Male patient, age 40–49; the lesion involves the back of the hand; an image taken at a distance: 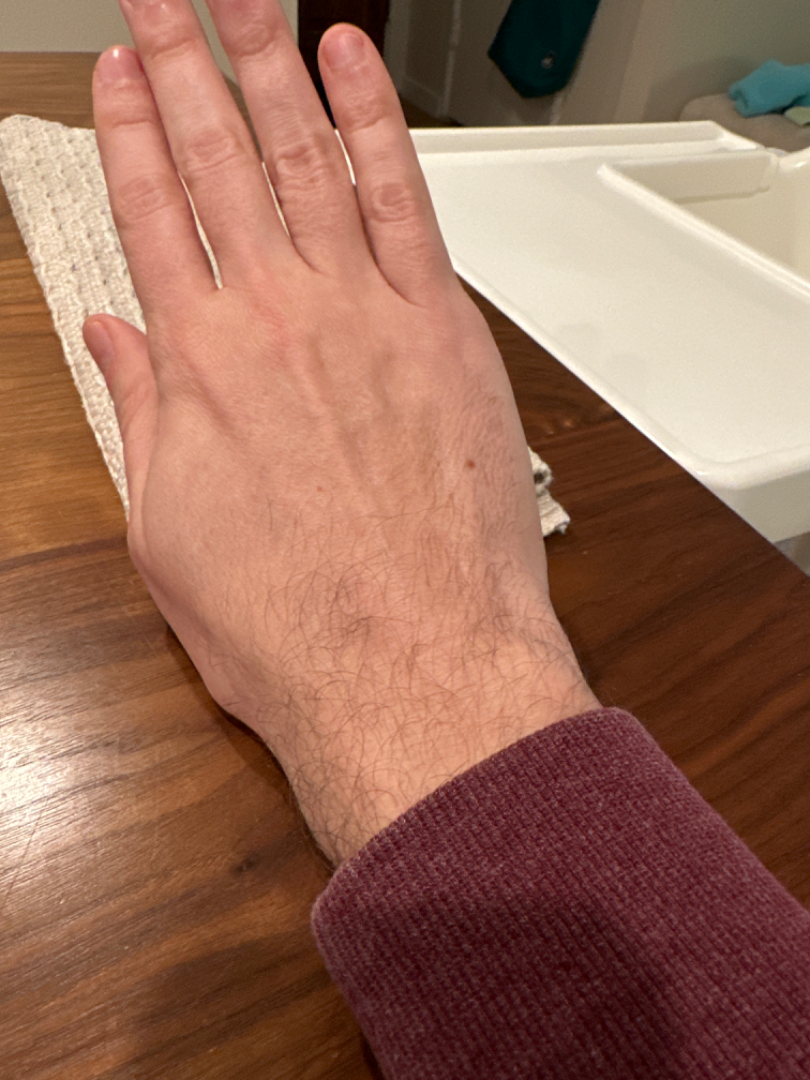{
  "symptoms": "none reported",
  "differential": {
    "tied_lead": [
      "Melanocytic Nevus",
      "Atypical Nevus"
    ]
  }
}